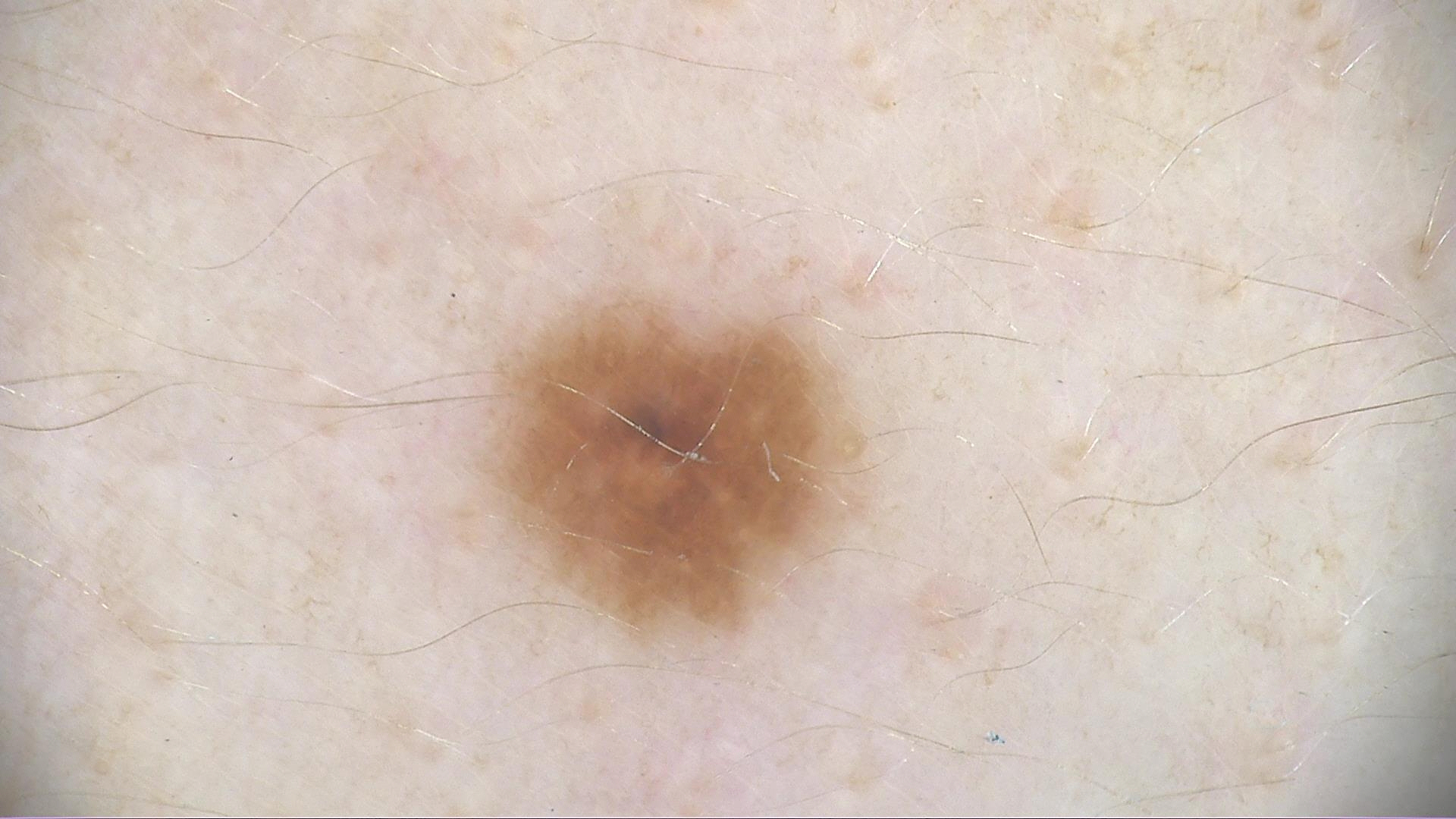Consistent with a dysplastic junctional nevus.